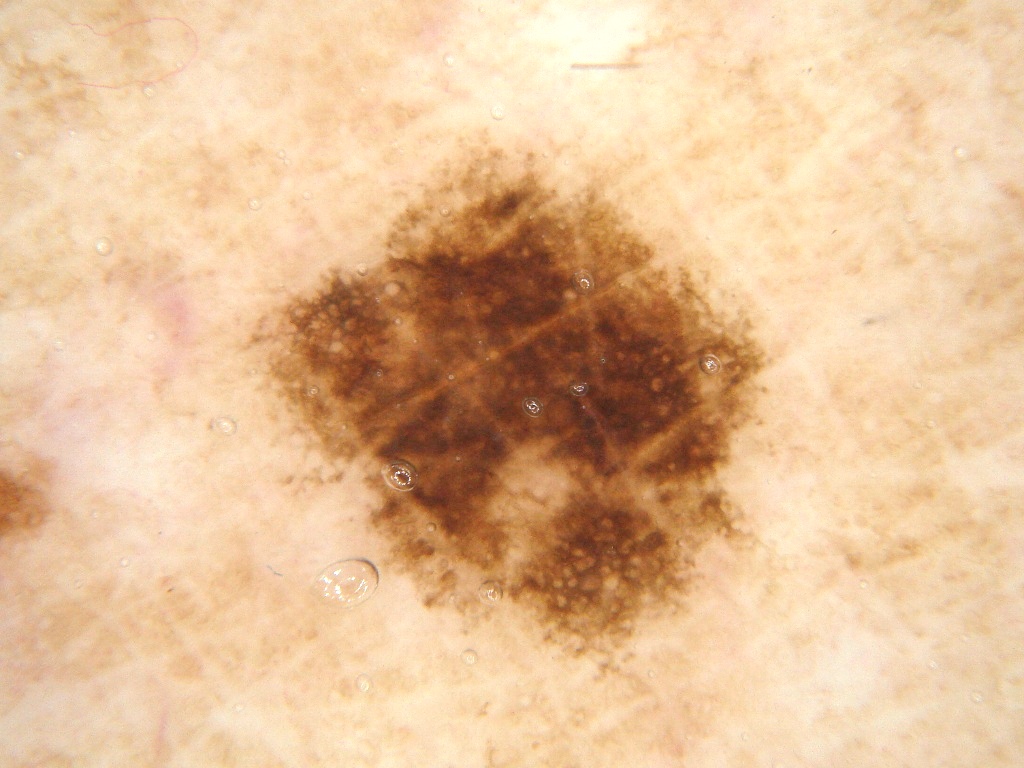Summary:
A dermoscopic view of a skin lesion. In (x1, y1, x2, y2) order, the lesion spans 221 126 788 704. Dermoscopic assessment notes no streaks or globules. A moderately sized lesion.
Impression:
The diagnostic assessment was a benign lesion.